Dermoscopy of a skin lesion.
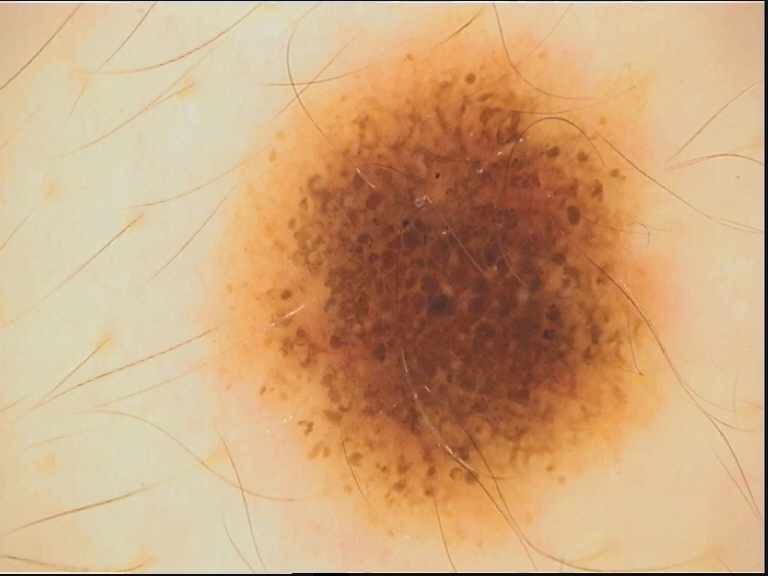<dermoscopy>
  <diagnosis>
    <name>dysplastic compound nevus</name>
    <code>cd</code>
    <malignancy>benign</malignancy>
    <super_class>melanocytic</super_class>
    <confirmation>expert consensus</confirmation>
  </diagnosis>
</dermoscopy>